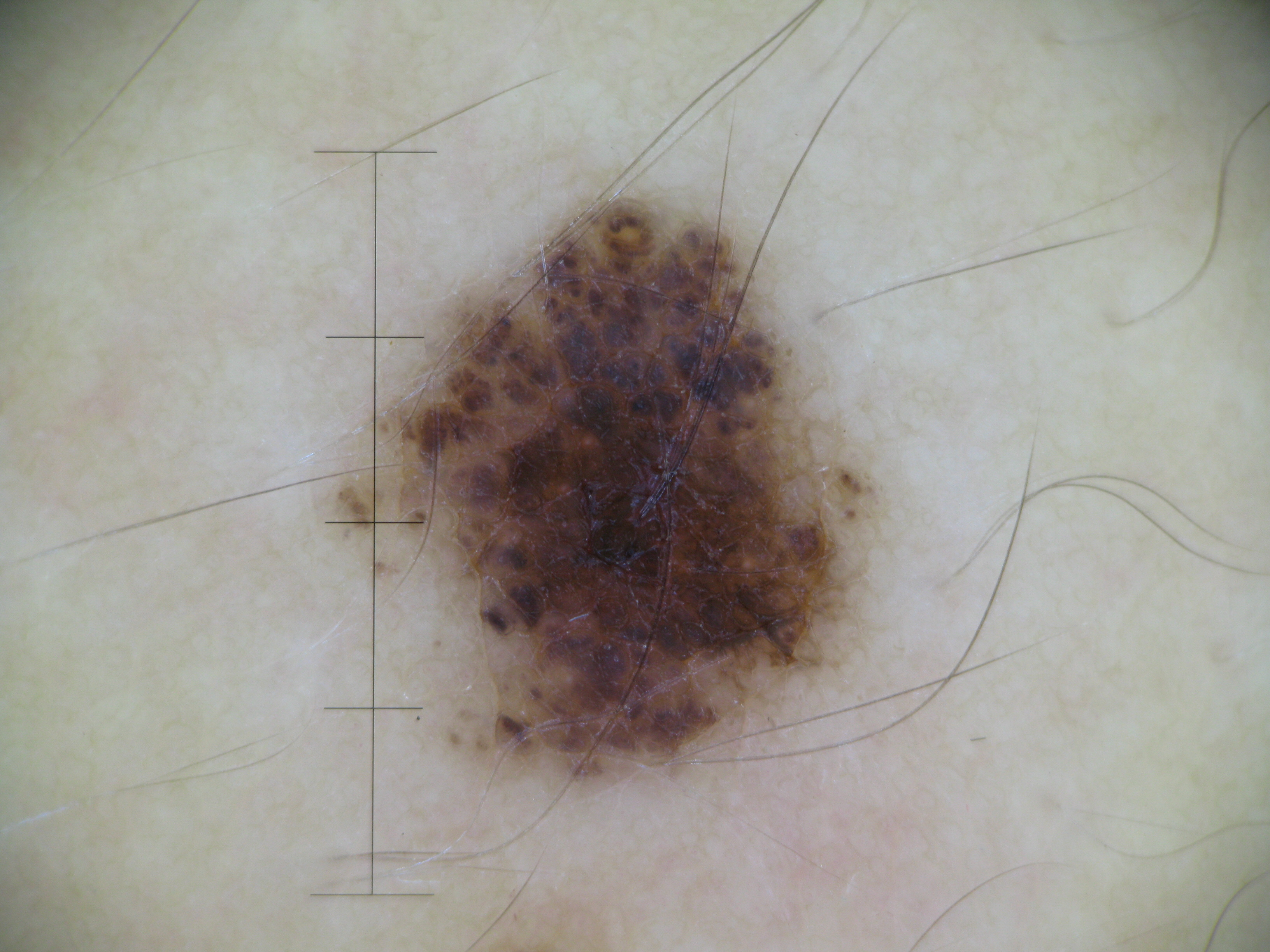Findings:
A dermoscopic close-up of a skin lesion.
Impression:
Classified as a banal lesion — a compound nevus.